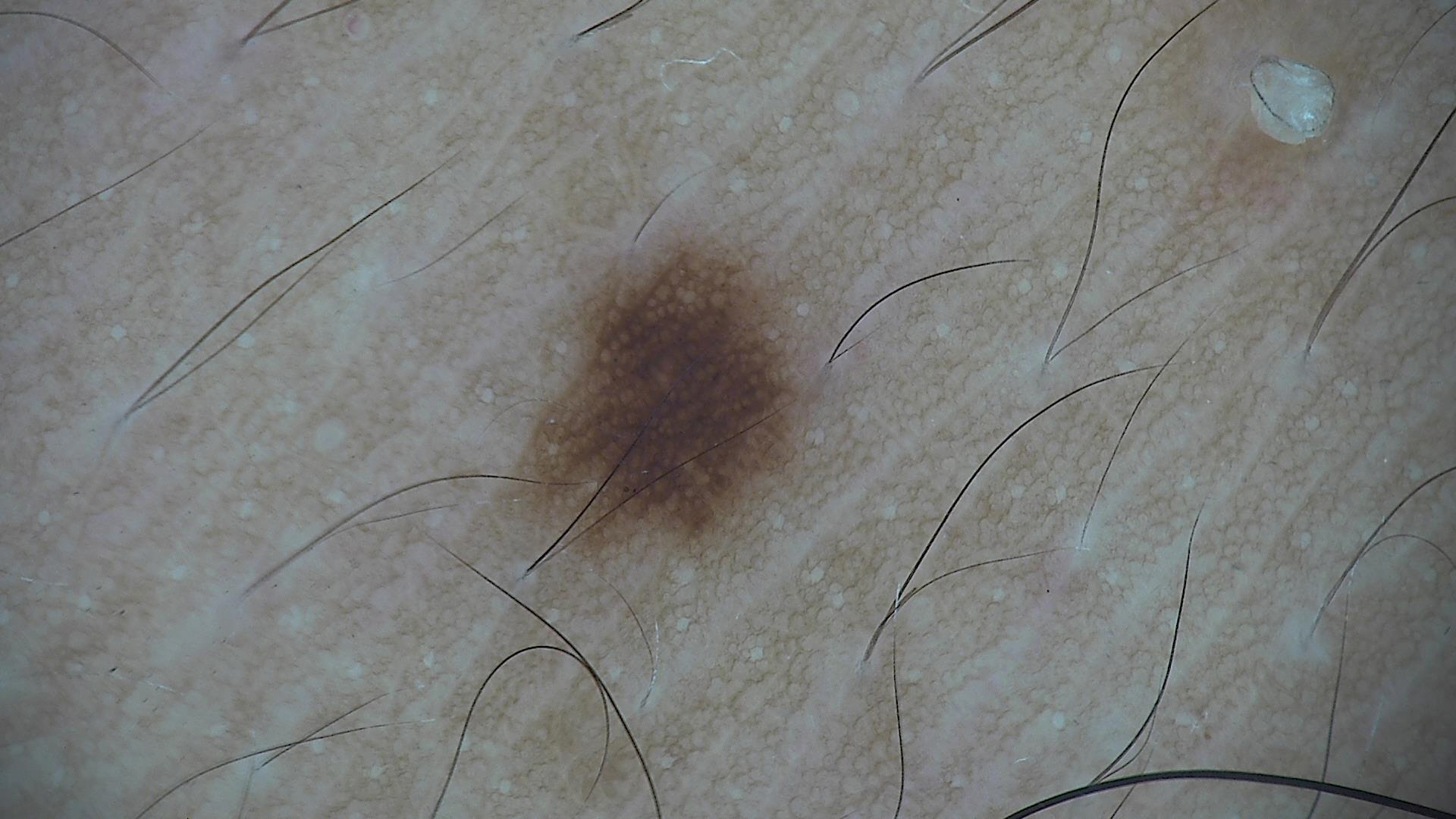Diagnosed as a dysplastic junctional nevus.